The lesion involves the palm · the photograph is a close-up of the affected area:
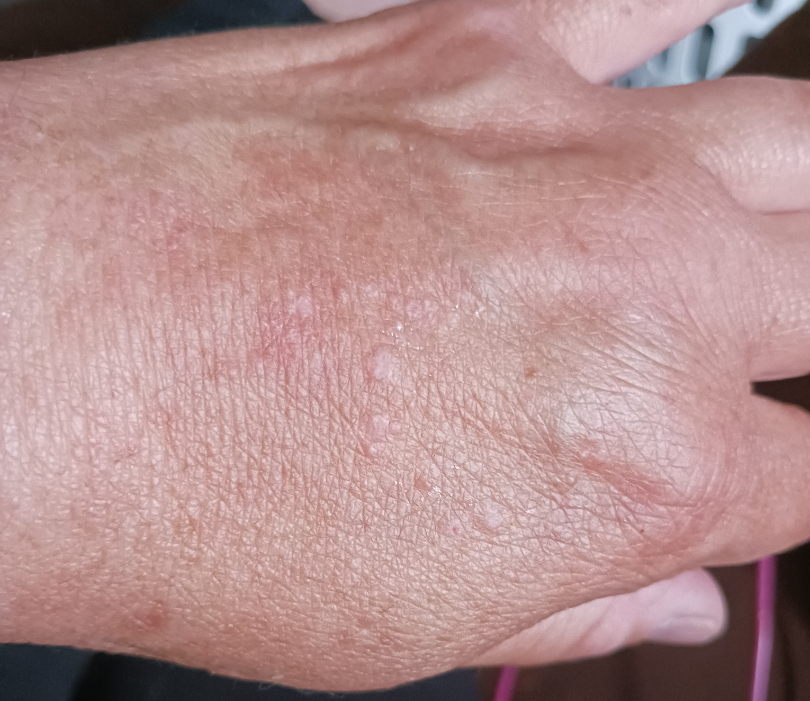Q: What was the assessment?
A: ungradable on photographic review